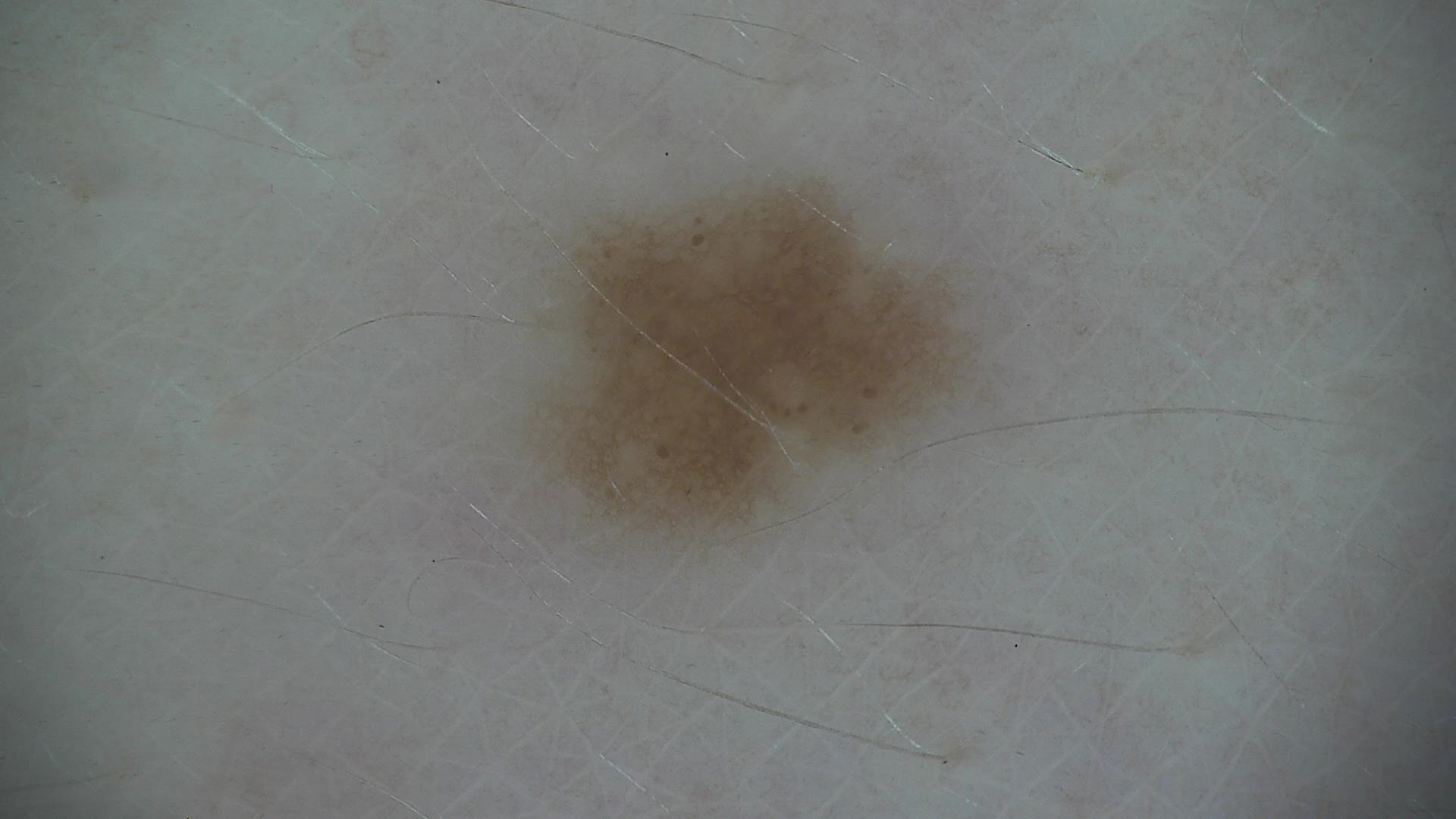Classified as a dysplastic junctional nevus.